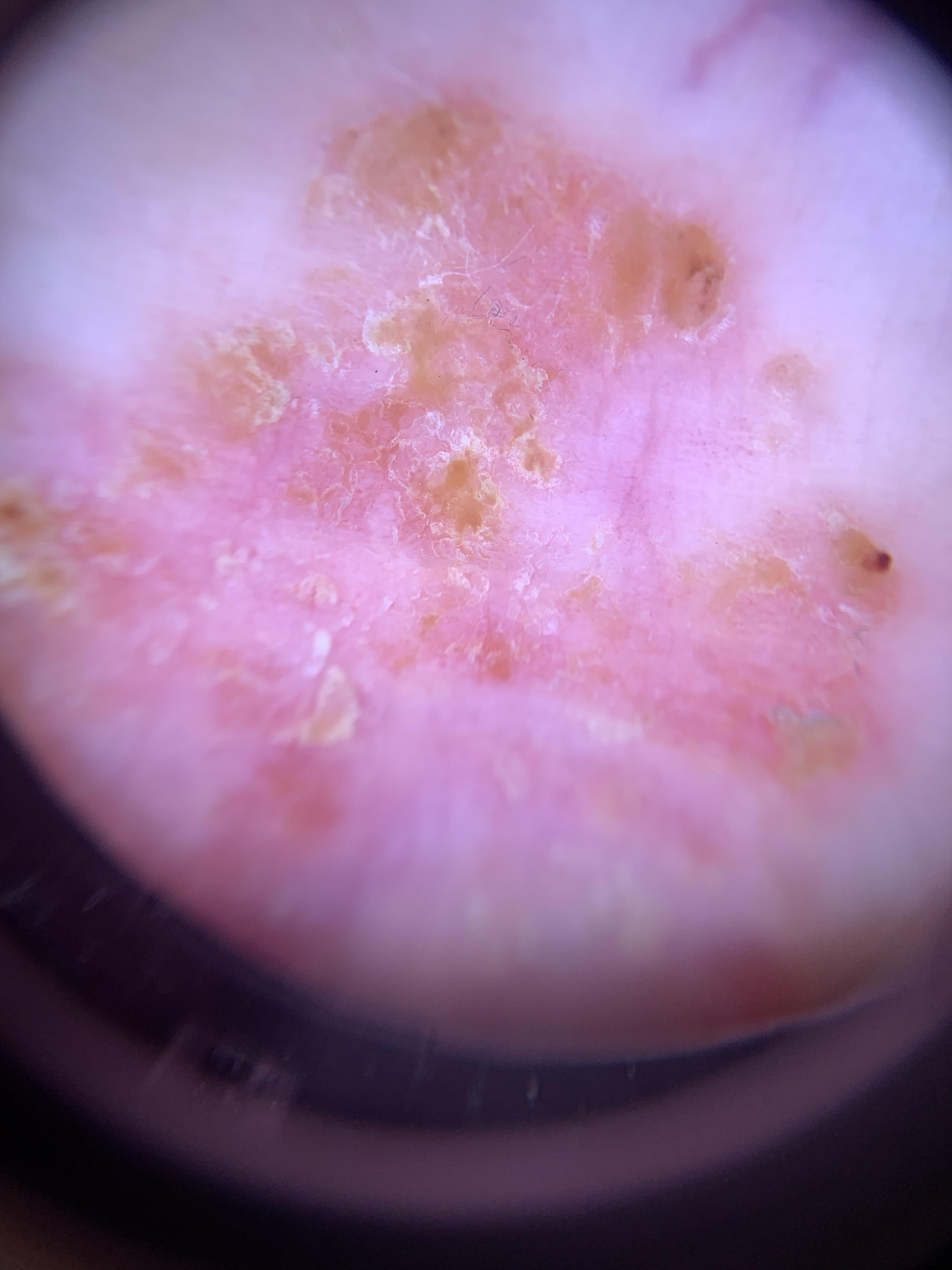Case:
– patient · male, in their mid- to late 80s or older
– Fitzpatrick · I
– modality · dermoscopy
– location · a lower extremity
– pathology · Squamous cell carcinoma (biopsy-proven)